A dermatoscopic image of a skin lesion:
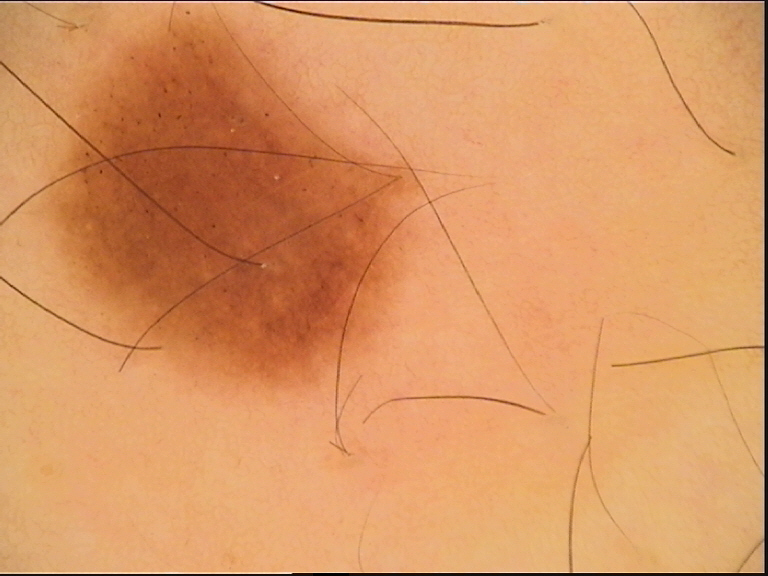Conclusion:
The diagnostic label was a benign lesion — a dysplastic junctional nevus.